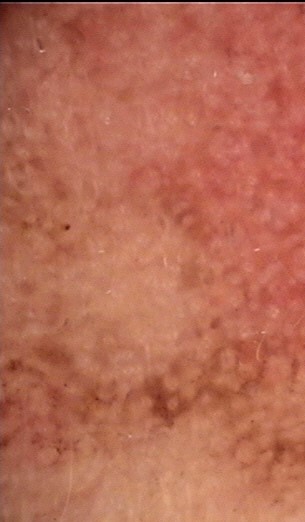<case>
  <diagnosis>
    <name>actinic keratosis</name>
    <code>ak</code>
    <malignancy>indeterminate</malignancy>
    <super_class>non-melanocytic</super_class>
    <confirmation>expert consensus</confirmation>
  </diagnosis>
</case>